Recorded as Fitzpatrick skin type II; a male subject aged around 25; an overview clinical photograph of a skin lesion:
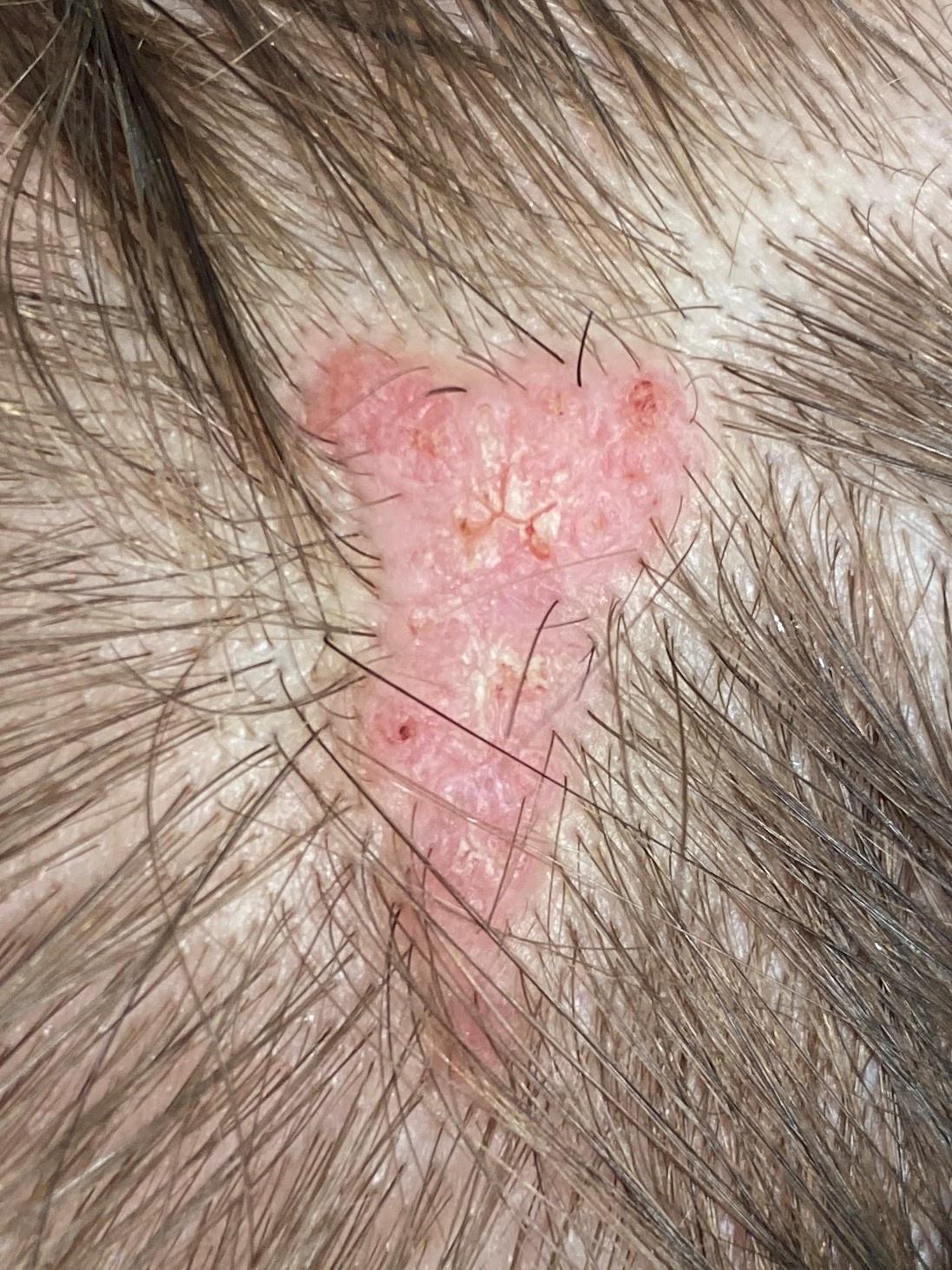The lesion is on the head or neck. Biopsy-confirmed as a benign lesion — a nevus.